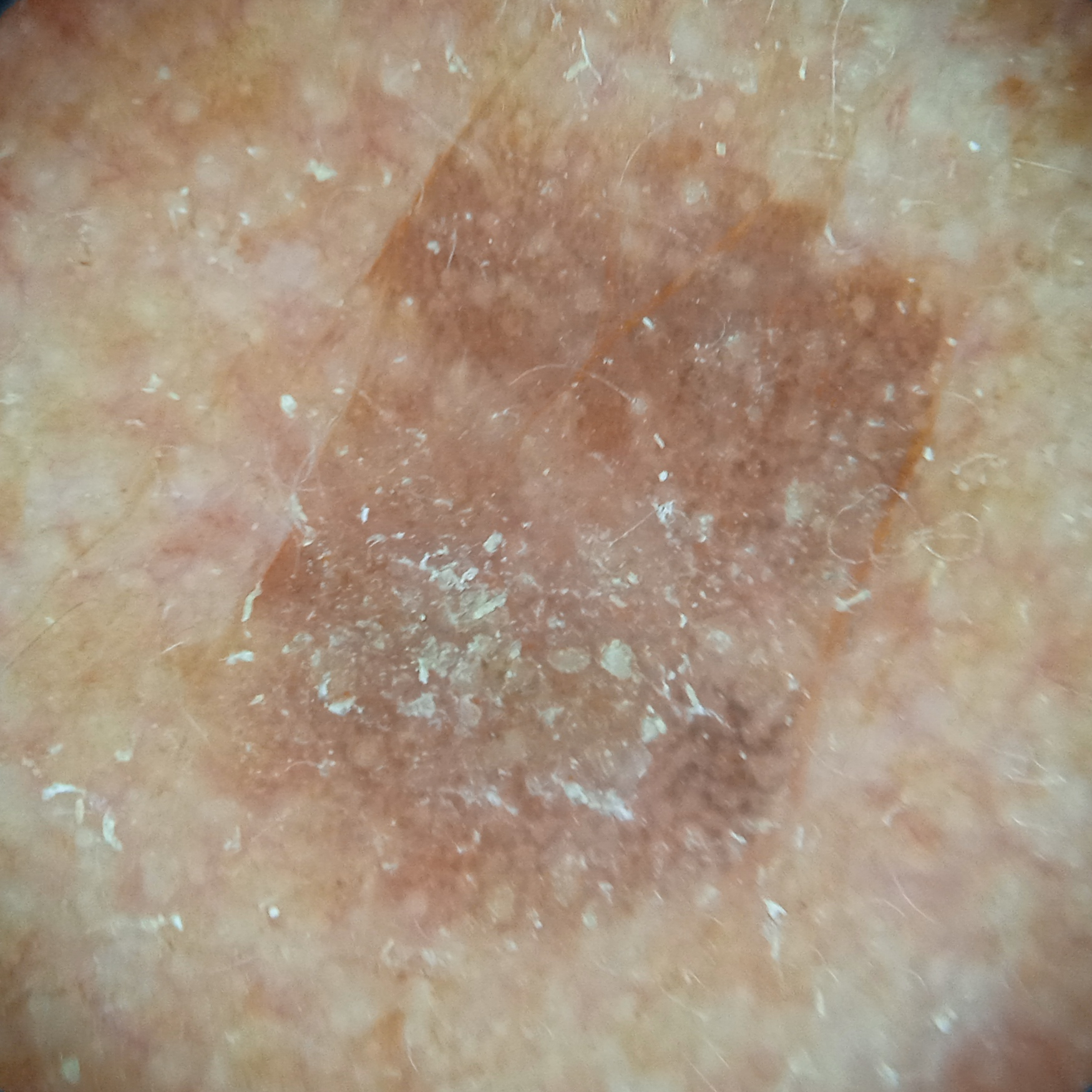A male patient age 76.
A dermoscopic image of a skin lesion.
The patient reports a personal history of skin cancer and a personal history of cancer.
The patient describes having few moles overall.
The lesion involves the face.
The lesion is about 8.7 mm across.
Histopathologically confirmed as a basal cell carcinoma, following excision, with a measured thickness of 2.5 mm.